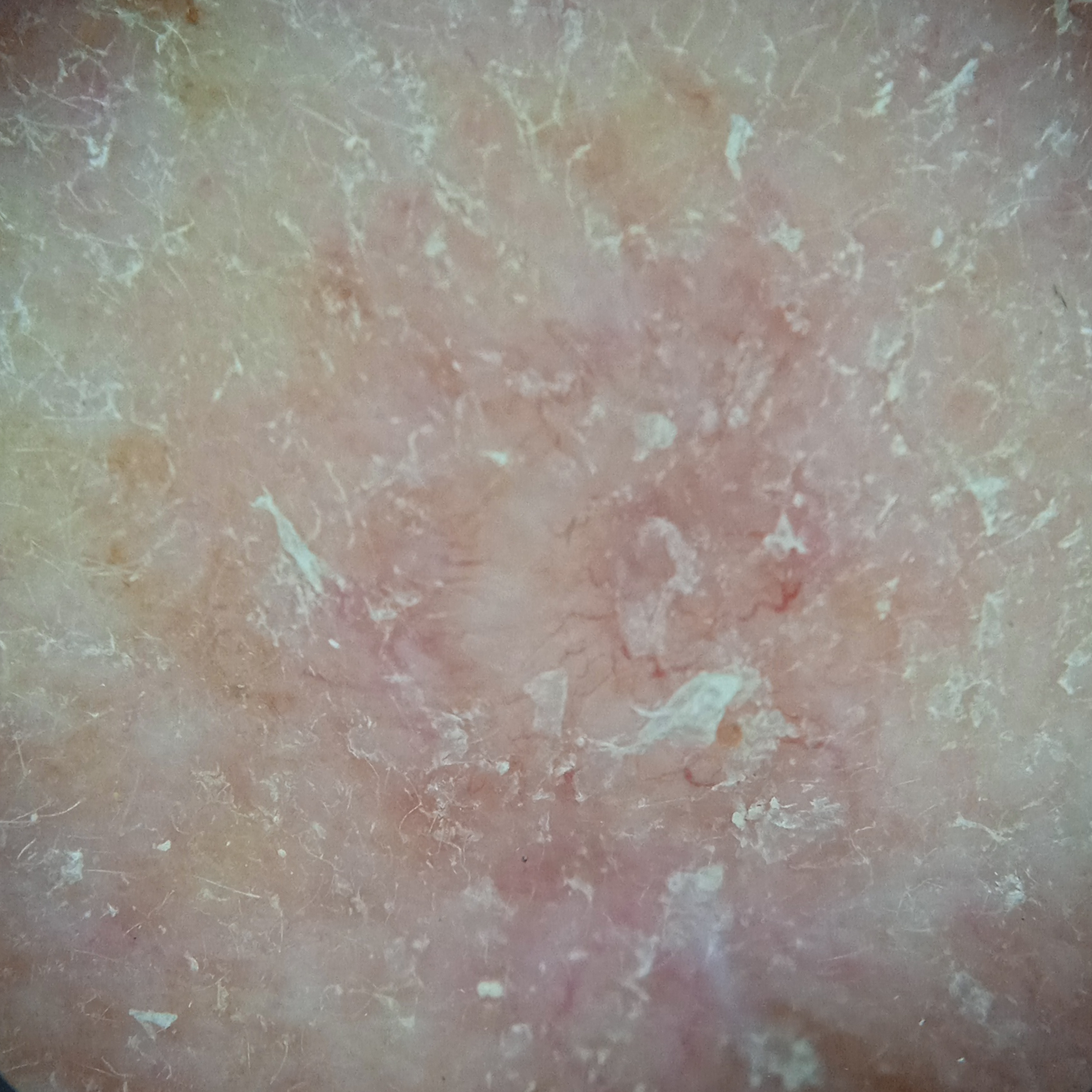Acquired for a research image collection, with no referral diagnosis.
A dermoscopic image of a skin lesion.
On a questionnaire the patient reported a family history of skin cancer, a personal history of cancer, no immunosuppression, and no sunbed use.
A female subject 92 years of age.
The patient says their skin tans without first burning.
The lesion is about 7 mm across.
The dermatologists' assessment was a basal cell carcinoma.